The subject is a female approximately 80 years of age; a skin lesion imaged with a dermatoscope — 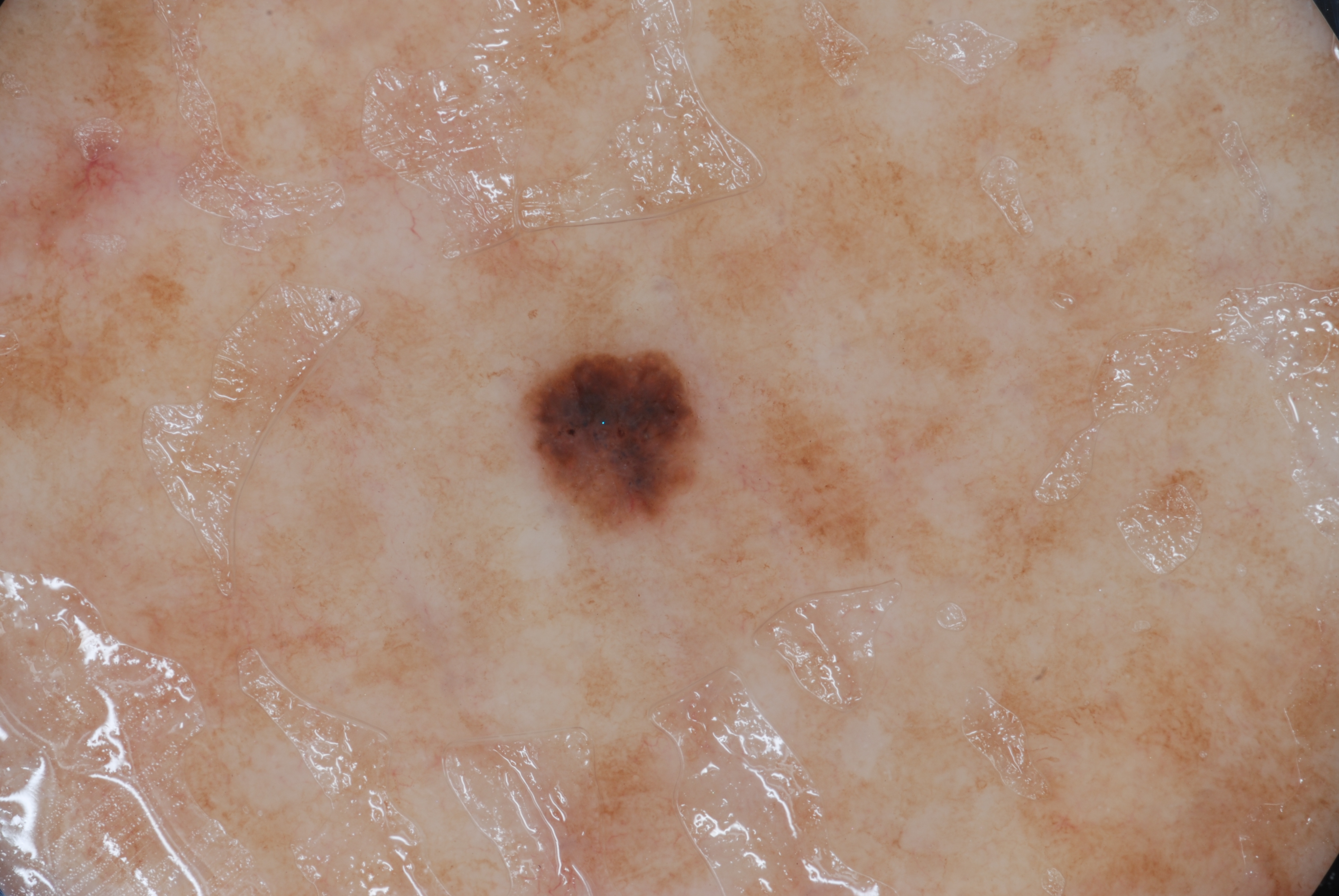Q: What dermoscopic features are present?
A: milia-like cysts; absent: pigment network, negative network, and streaks
Q: What is the lesion's bounding box?
A: [517, 332, 708, 534]
Q: What did the assessment conclude?
A: a seborrheic keratosis, a benign lesion